Texture is reported as raised or bumpy · located on the arm · the condition has been present for about one day · the photo was captured at a distance — 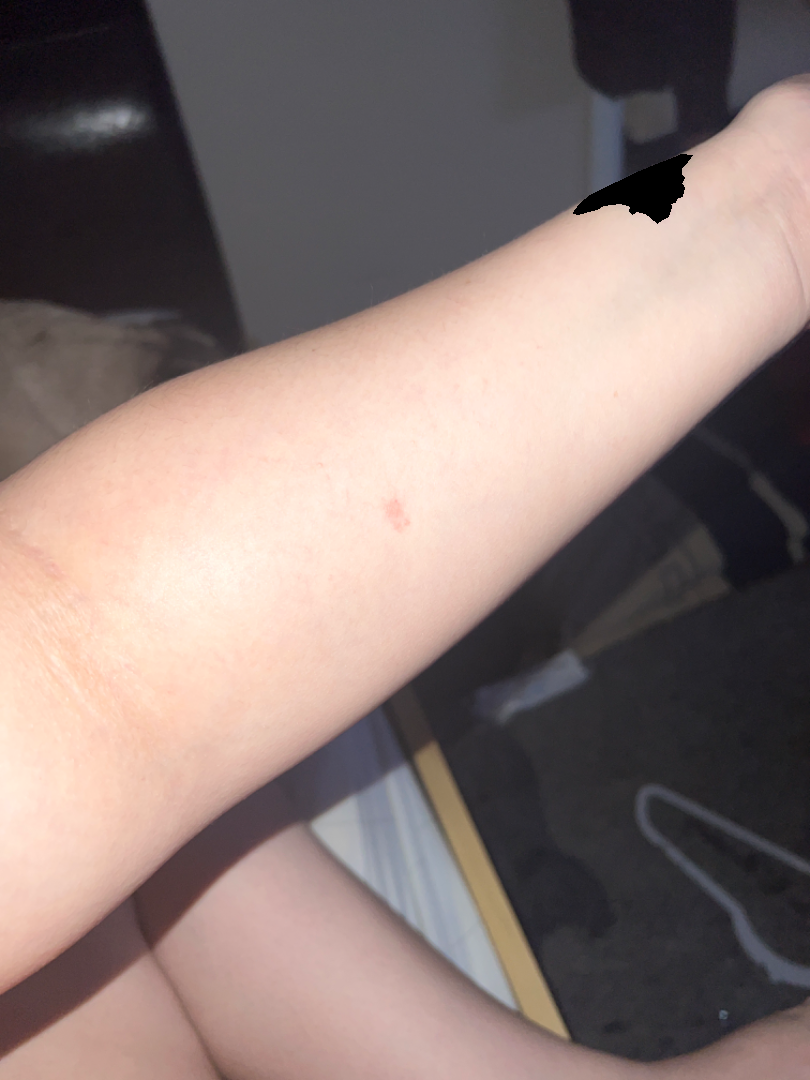Notes:
– impression: Eczema (1.00)